A dermatoscopic image of a skin lesion: 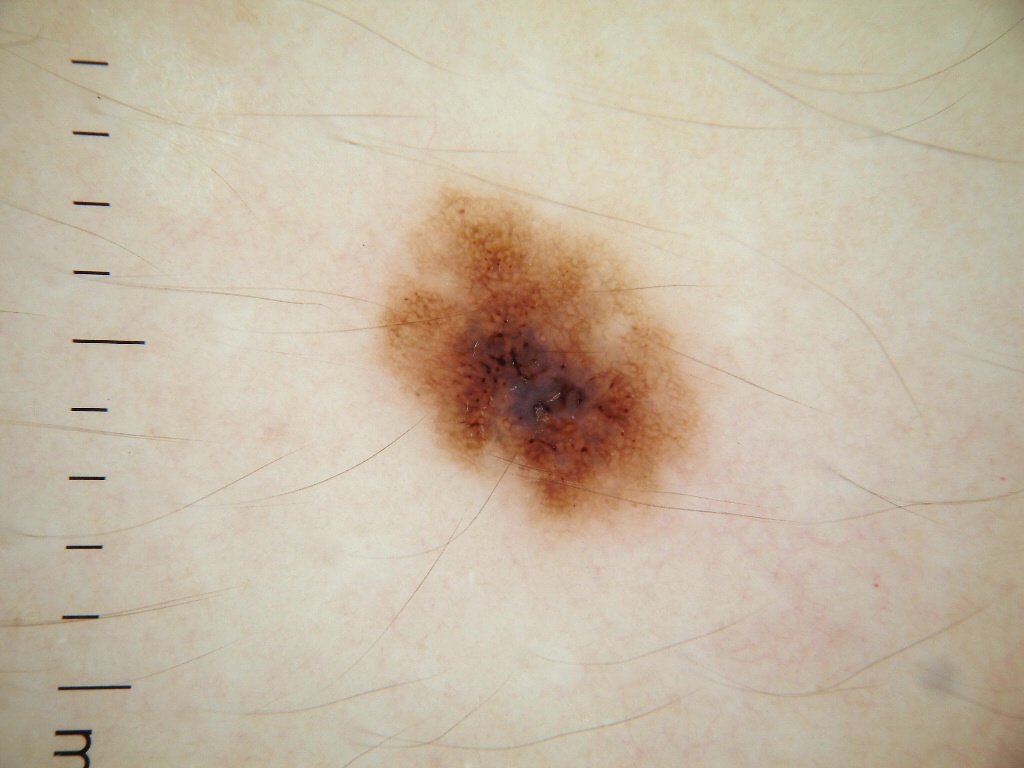As (left, top, right, bottom), the lesion occupies the region box(374, 186, 705, 538). Dermoscopic assessment notes globules and pigment network. Consistent with a melanocytic nevus.